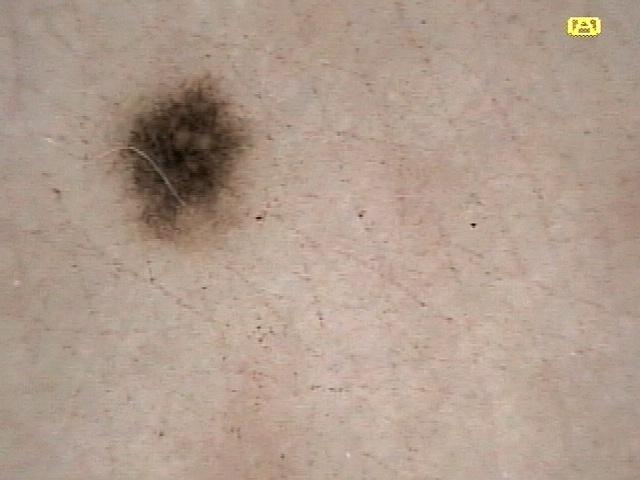Q: What are the patient's age and sex?
A: female, approximately 50 years of age
Q: What kind of image is this?
A: contact-polarized dermoscopy
Q: What is the anatomic site?
A: a lower extremity
Q: What is this lesion?
A: Nevus (clinical impression)